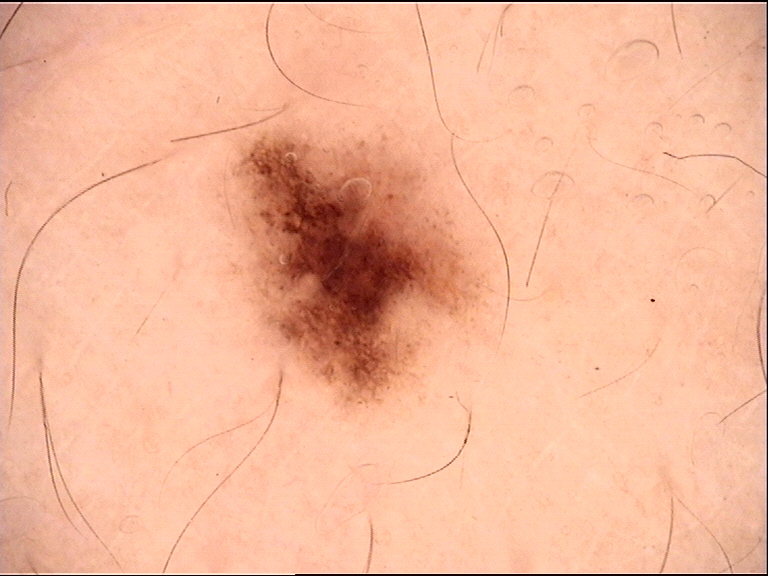<dermoscopy>
  <diagnosis>
    <name>dysplastic junctional nevus</name>
    <code>jd</code>
    <malignancy>benign</malignancy>
    <super_class>melanocytic</super_class>
    <confirmation>expert consensus</confirmation>
  </diagnosis>
</dermoscopy>